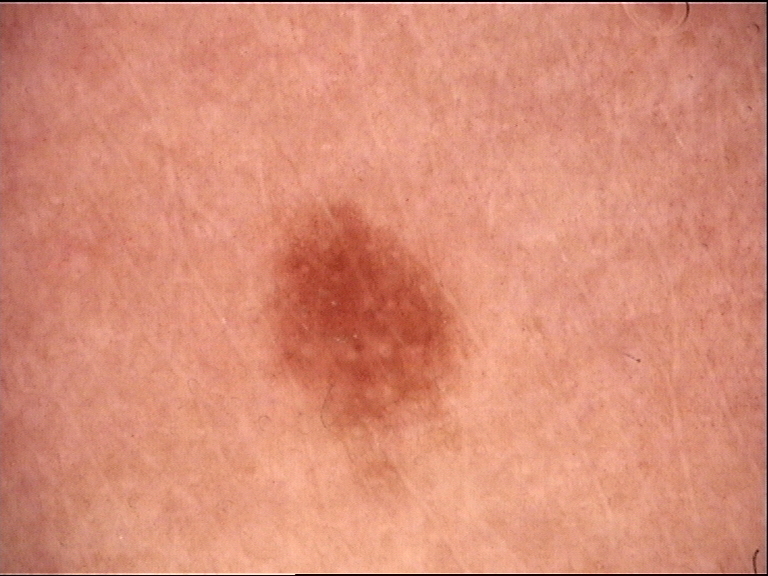A skin lesion imaged with a dermatoscope. Diagnosed as a junctional nevus.